A close-up photograph · the arm is involved · the patient is 50–59, female — 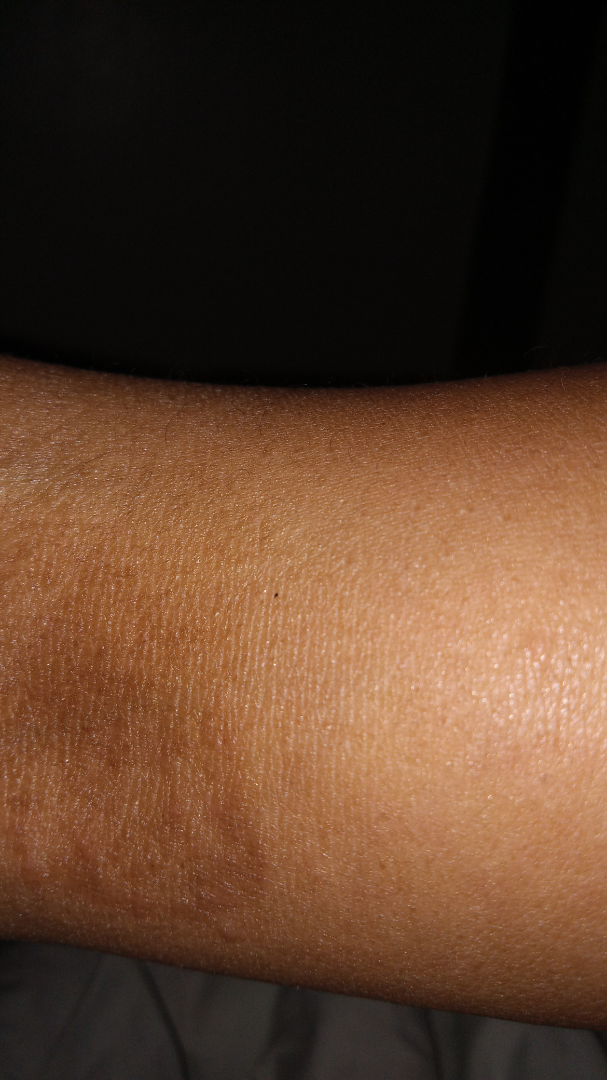Q: Fitzpatrick or Monk tone?
A: lay graders estimated Monk Skin Tone 4 or 6 (two reviewer pools disagreed)
Q: When did this start?
A: less than one week
Q: What is the lesion texture?
A: raised or bumpy
Q: What is the differential diagnosis?
A: Lichenified eczematous dermatitis (weight 0.23); Chronic dermatitis (weight 0.23); Tinea (weight 0.19); Eczema (weight 0.17); Post-Inflammatory hyperpigmentation (weight 0.17)